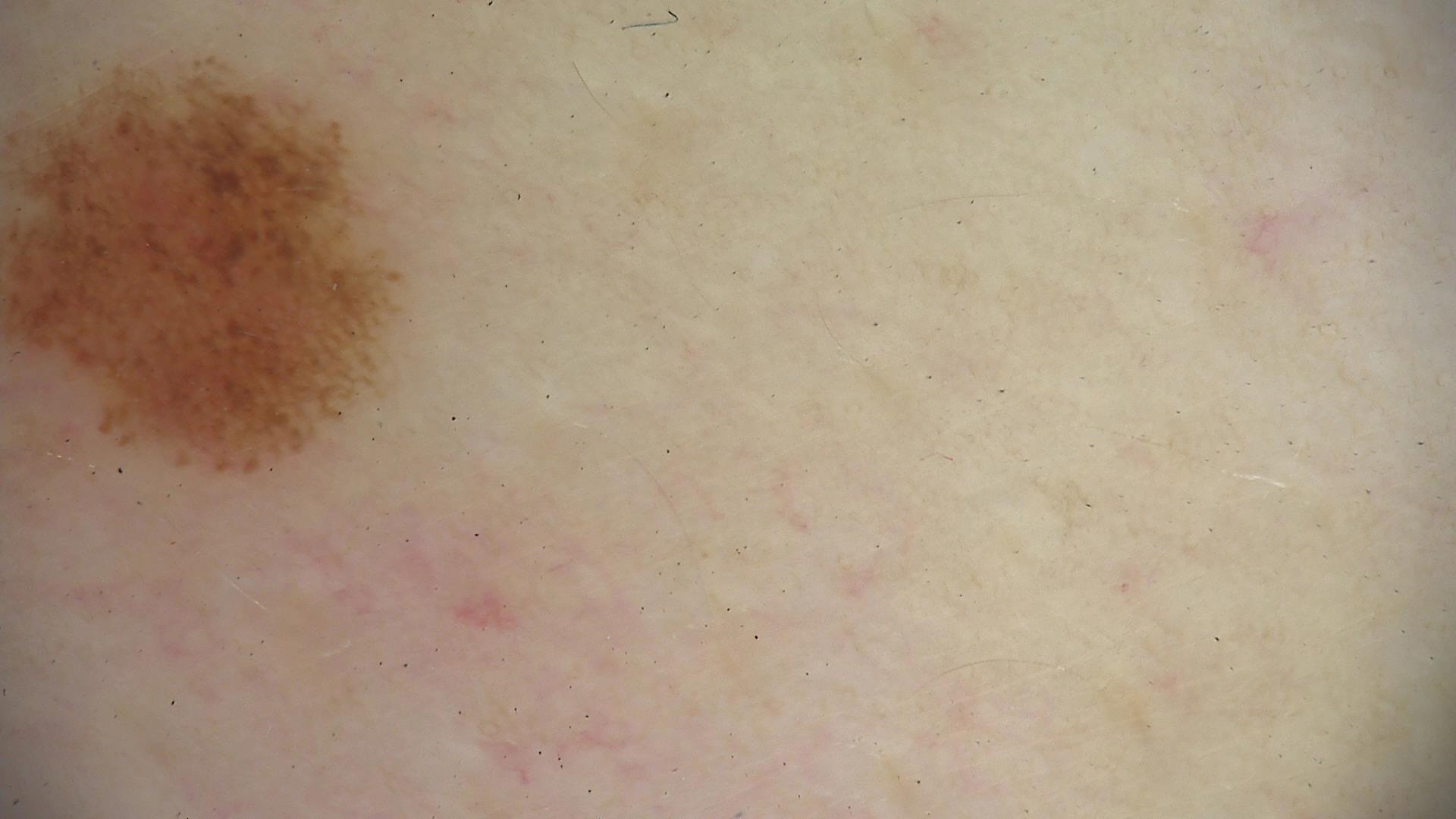Findings: A dermoscopic image of a skin lesion. Conclusion: The diagnostic label was a dysplastic junctional nevus.